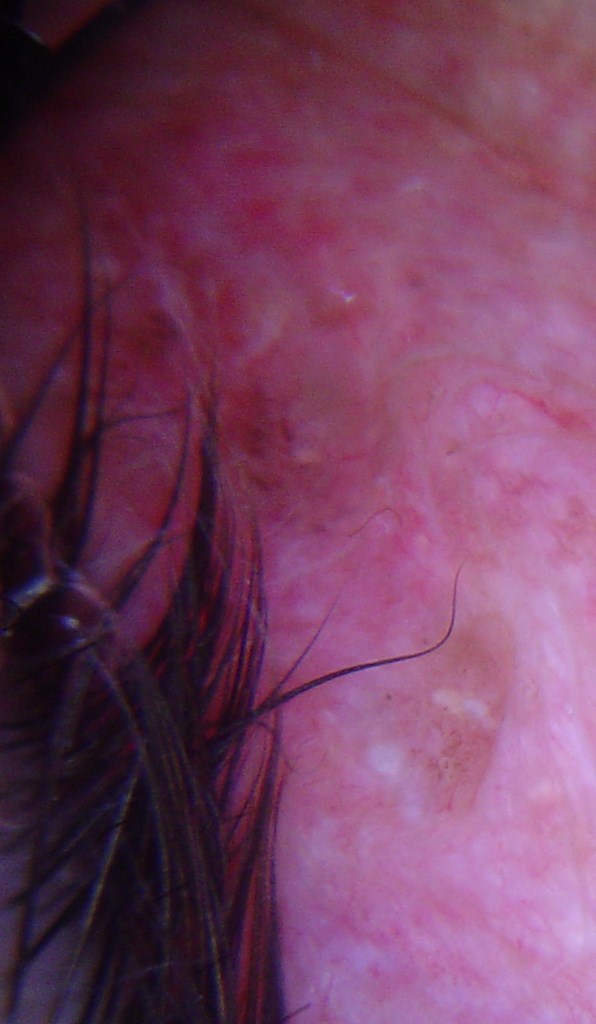<dermoscopy>
<image>dermatoscopy</image>
<lesion_type>
<main_class>keratinocytic</main_class>
</lesion_type>
<diagnosis>
<name>basal cell carcinoma</name>
<code>bcc</code>
<malignancy>malignant</malignancy>
<super_class>non-melanocytic</super_class>
<confirmation>histopathology</confirmation>
</diagnosis>
</dermoscopy>